The patient is male. The photo was captured at an angle. The back of the hand is involved: 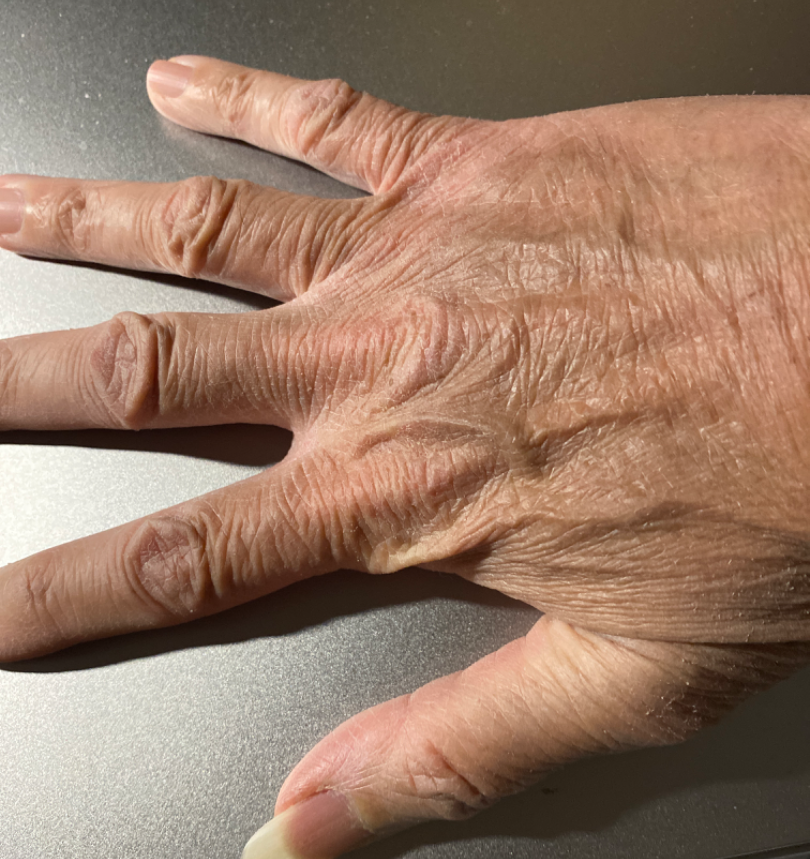Findings:
* lesion texture · flat and rough or flaky
* clinical impression · Eczema (possible); Xerosis (possible); Tinea (possible)